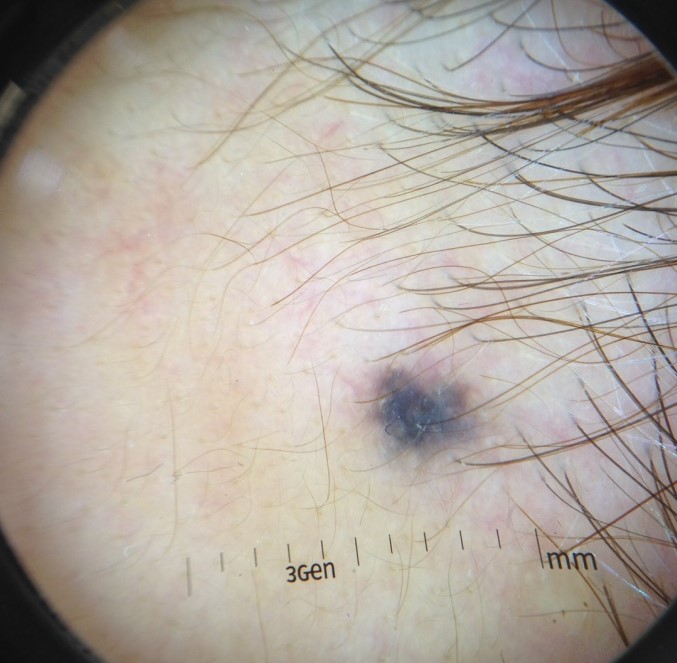Findings:
Dermoscopy of a skin lesion.
Impression:
Labeled as a blue nevus.